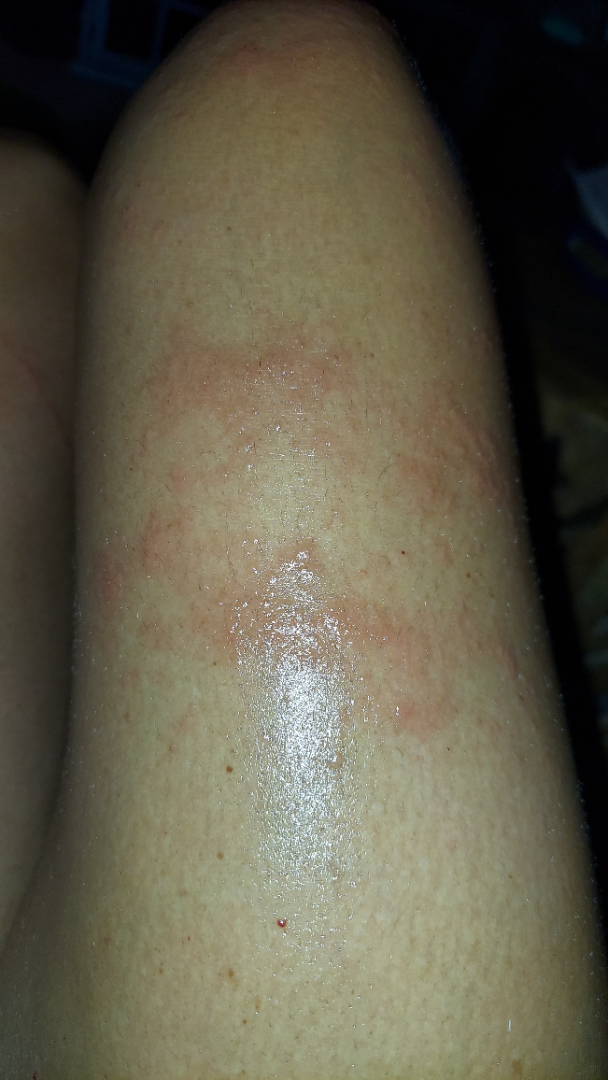{
  "body_site": "leg",
  "patient": "female, age 40–49",
  "shot_type": "close-up",
  "differential": {
    "leading": [
      "Allergic Contact Dermatitis"
    ],
    "unlikely": [
      "Phytophotodermatitis",
      "Herpes Zoster",
      "Urticaria",
      "Insect Bite"
    ]
  }
}